A moderate number of moles by the patient's own estimate; a dermoscopy image of a skin lesion; the referring clinician suspected melanocytic nevus; the patient says their skin reddens with sun exposure; a female subject 59 years old: 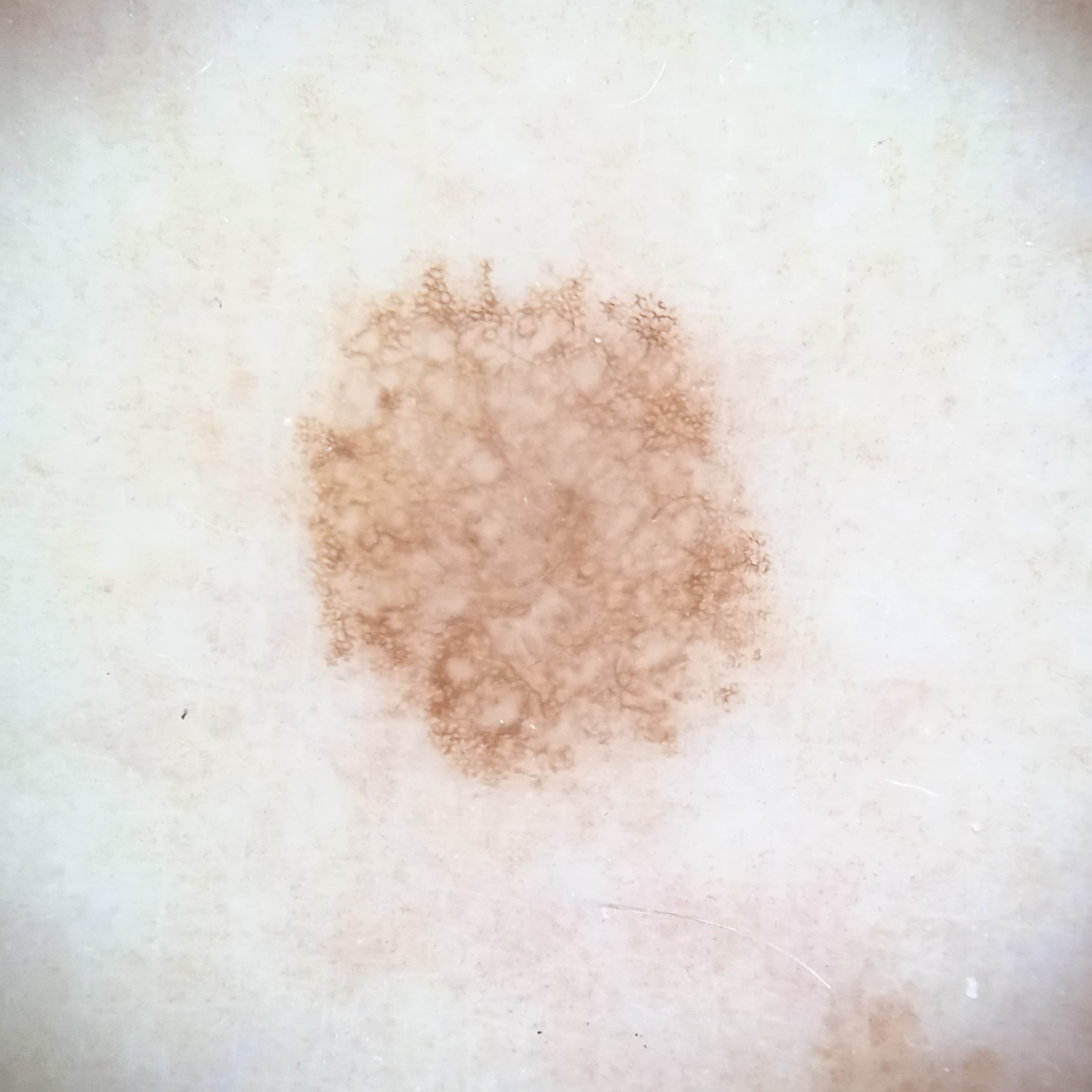The lesion is on an arm. The lesion is about 6.7 mm across. The biopsy diagnosis was an atypical (dysplastic) nevus, following excision.